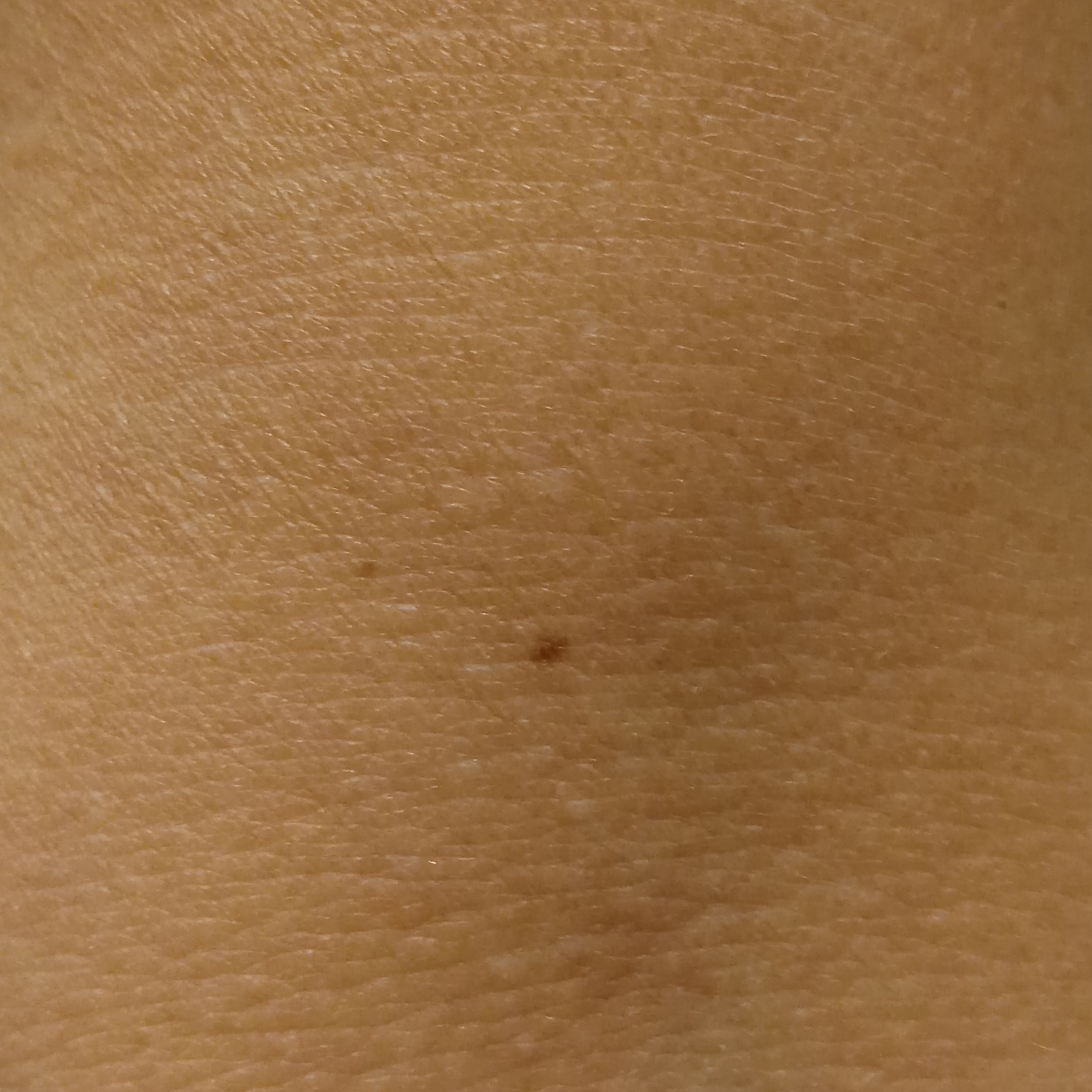Findings: A clinical photograph of a skin lesion. Acquired for a research image collection, with no referral diagnosis. The patient says their skin tans without first burning. The lesion measures approximately 1.9 mm. Assessment: The diagnostic impression was a melanocytic nevus.